A dermoscopic view of a skin lesion; a male subject, aged around 40 — 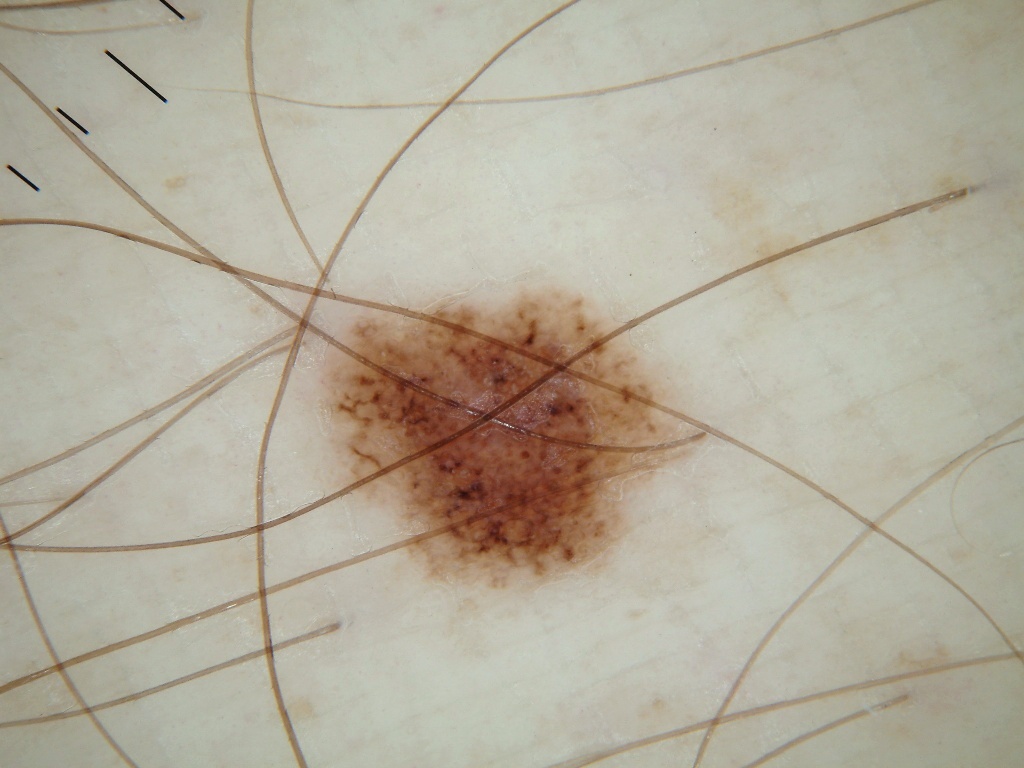- size — moderate
- lesion location — [303,268,710,608]
- dermoscopic features not present — milia-like cysts, streaks, globules, negative network, and pigment network
- diagnostic label — a melanocytic nevus